An image taken at a distance; the lesion involves the back of the hand; reported duration is about one day; the patient also reports fatigue; self-categorized by the patient as a rash; the lesion is associated with bothersome appearance and itching; the contributor is 18–29, female.
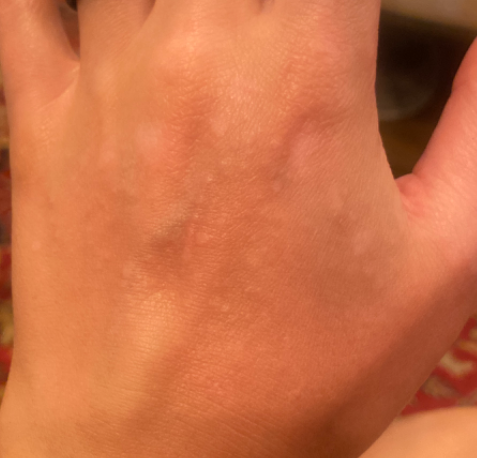diagnostic considerations = most likely Post-Inflammatory hypopigmentation.